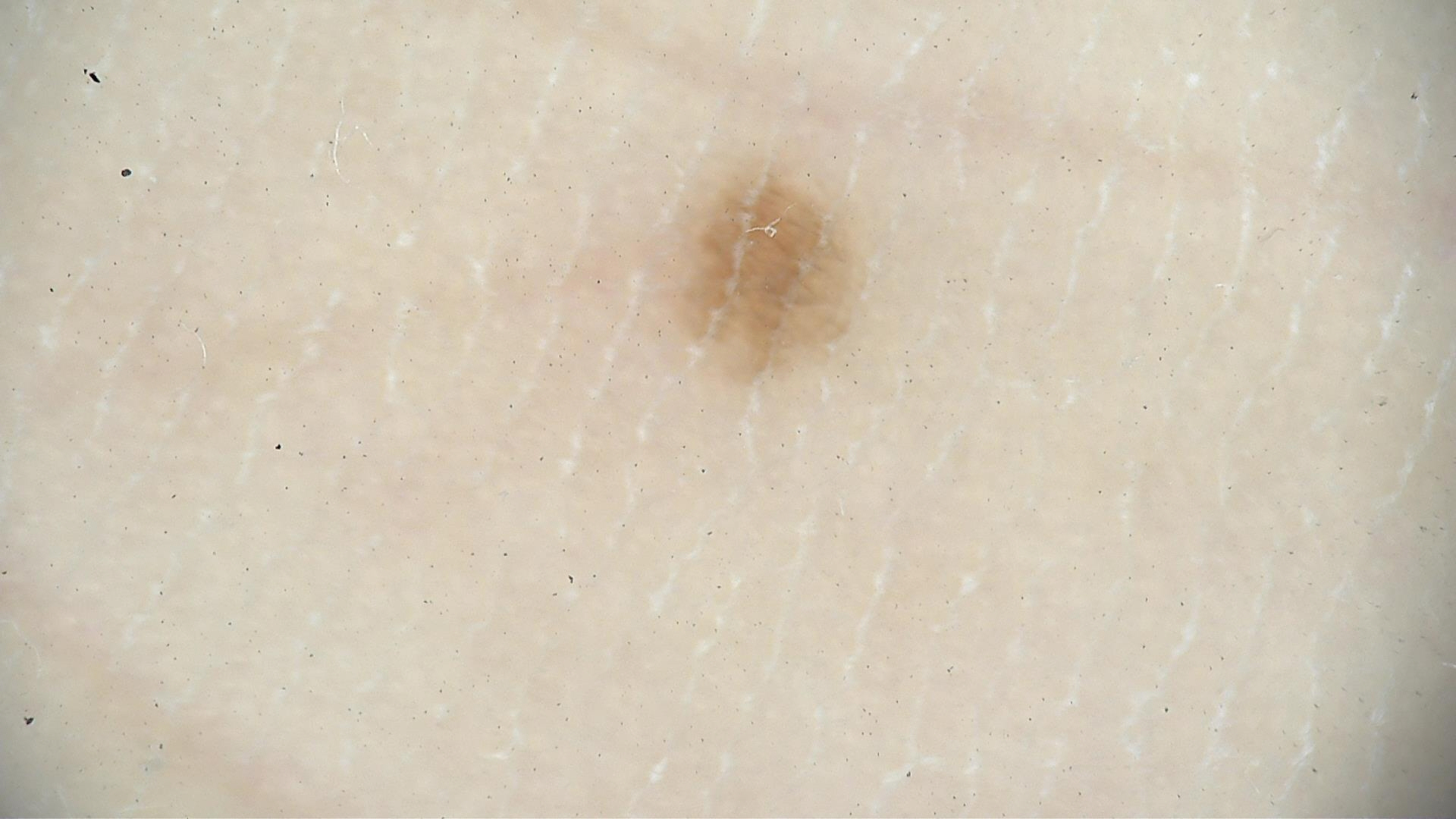Dermoscopy of a skin lesion. Diagnosed as an acral dysplastic junctional nevus.